A skin lesion imaged with a dermatoscope.
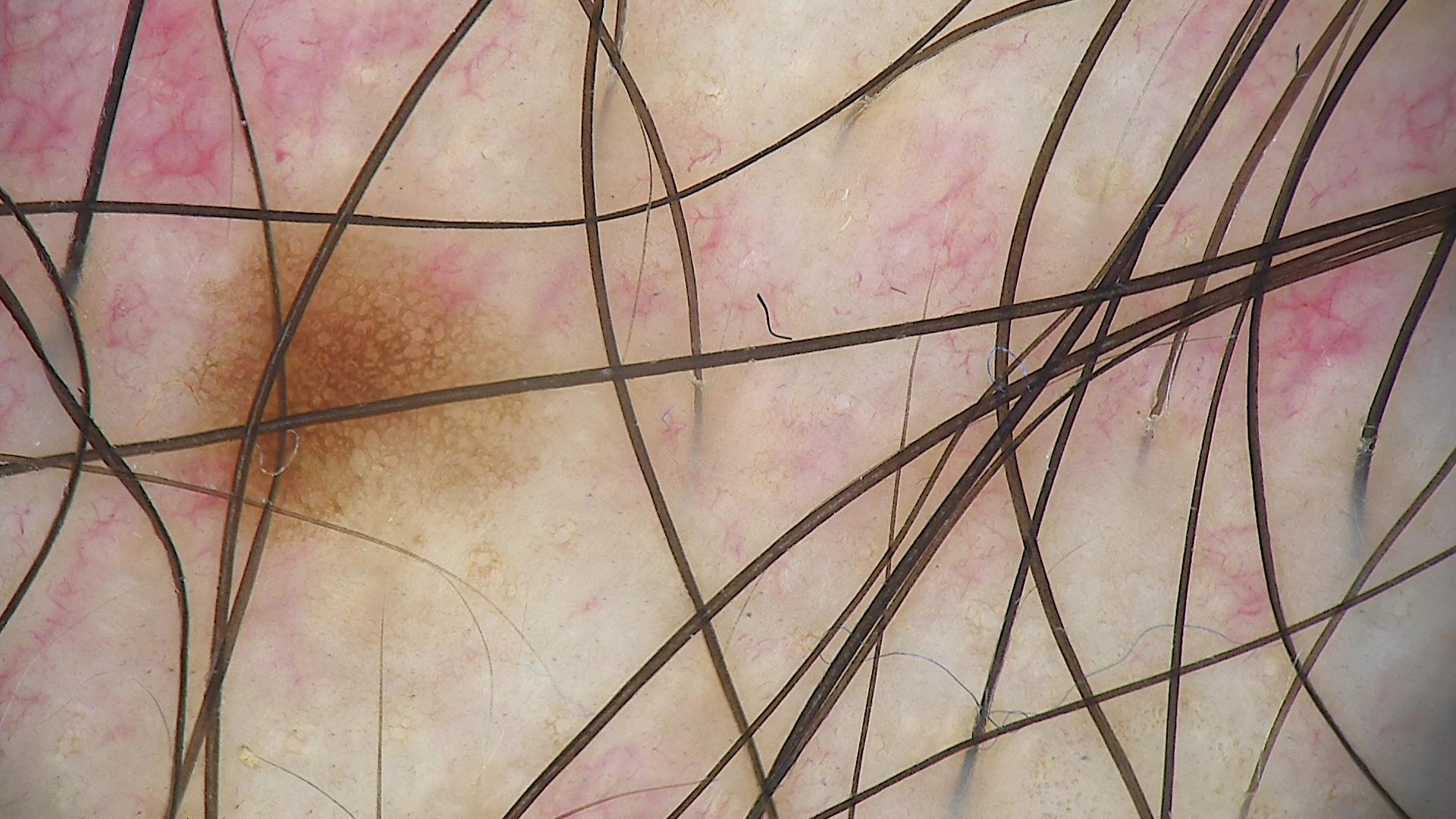subtype = banal; diagnosis = junctional nevus (expert consensus).